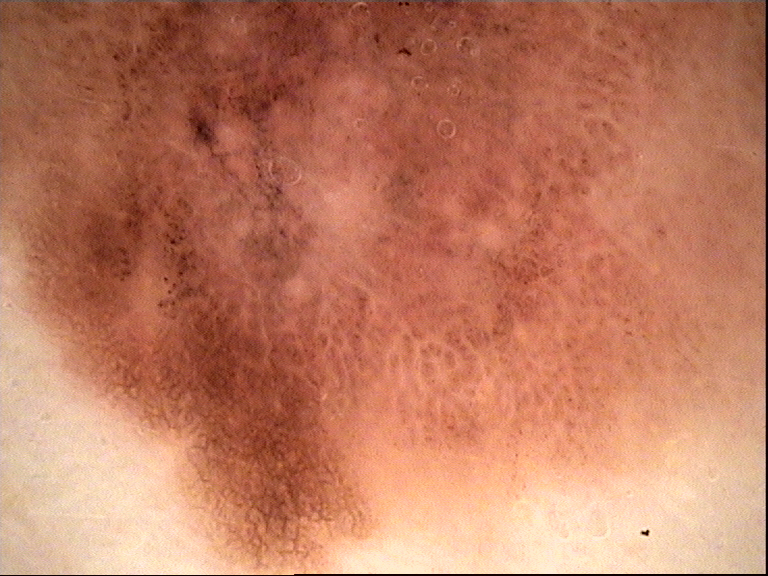image type = dermatoscopy
label = acral lentiginous melanoma (biopsy-proven)